A dermatoscopic image of a skin lesion.
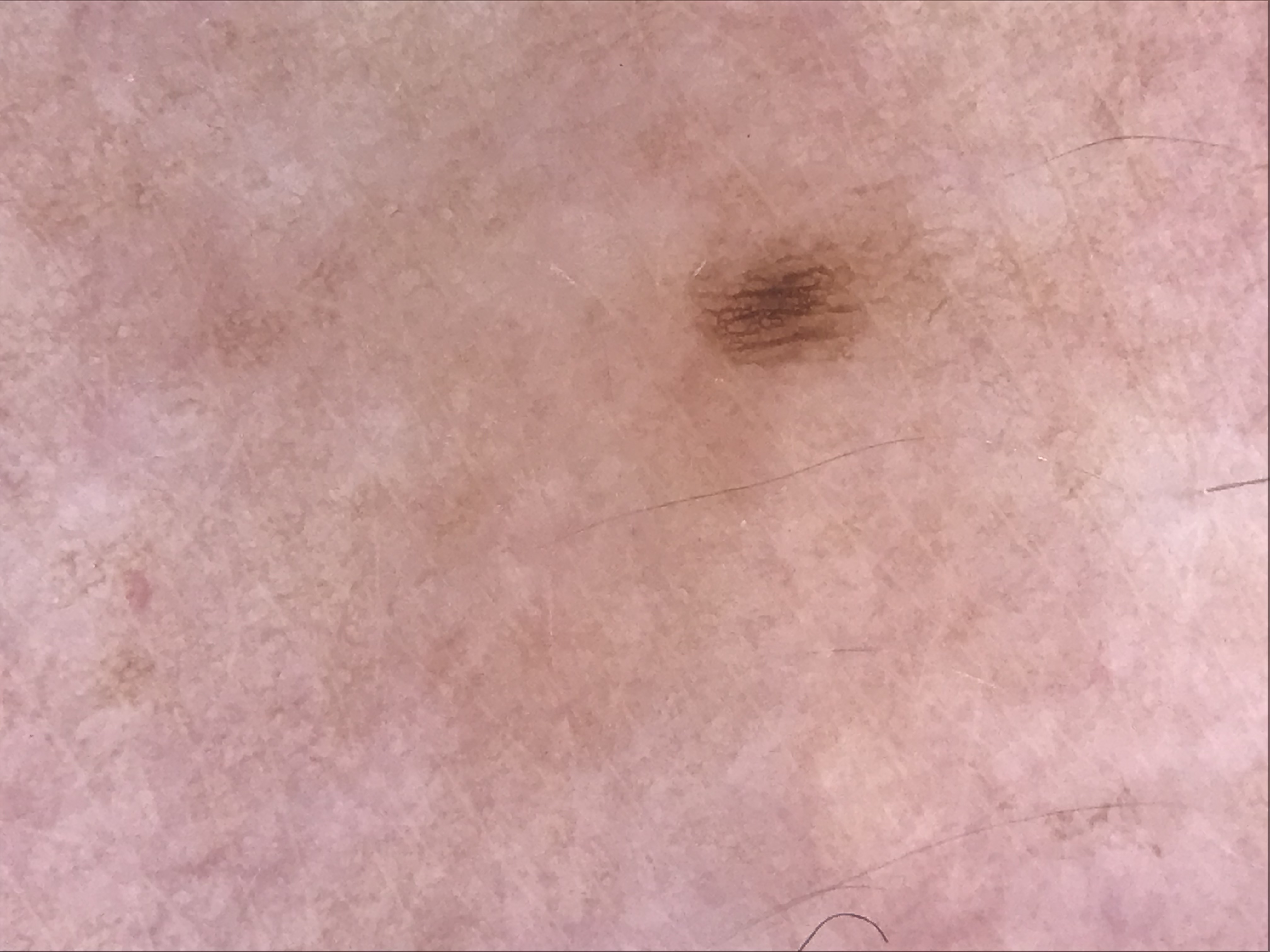{
  "lesion_type": {
    "main_class": "banal",
    "pattern": "junctional"
  },
  "diagnosis": {
    "name": "junctional nevus",
    "code": "jb",
    "malignancy": "benign",
    "super_class": "melanocytic",
    "confirmation": "expert consensus"
  }
}